An image taken at a distance · Fitzpatrick phototype V; lay reviewers estimated a MST of 2: 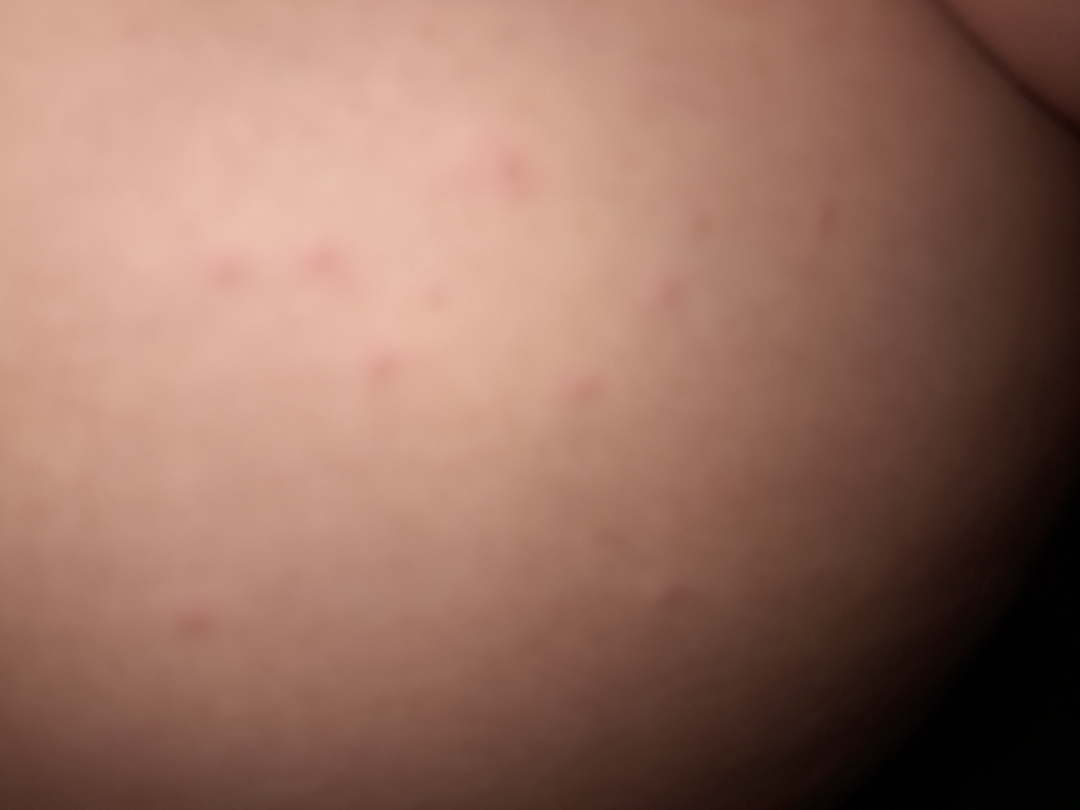differential:
  leading:
    - Folliculitis
  considered:
    - Eczema
    - Molluscum Contagiosum